A skin lesion imaged with a dermatoscope.
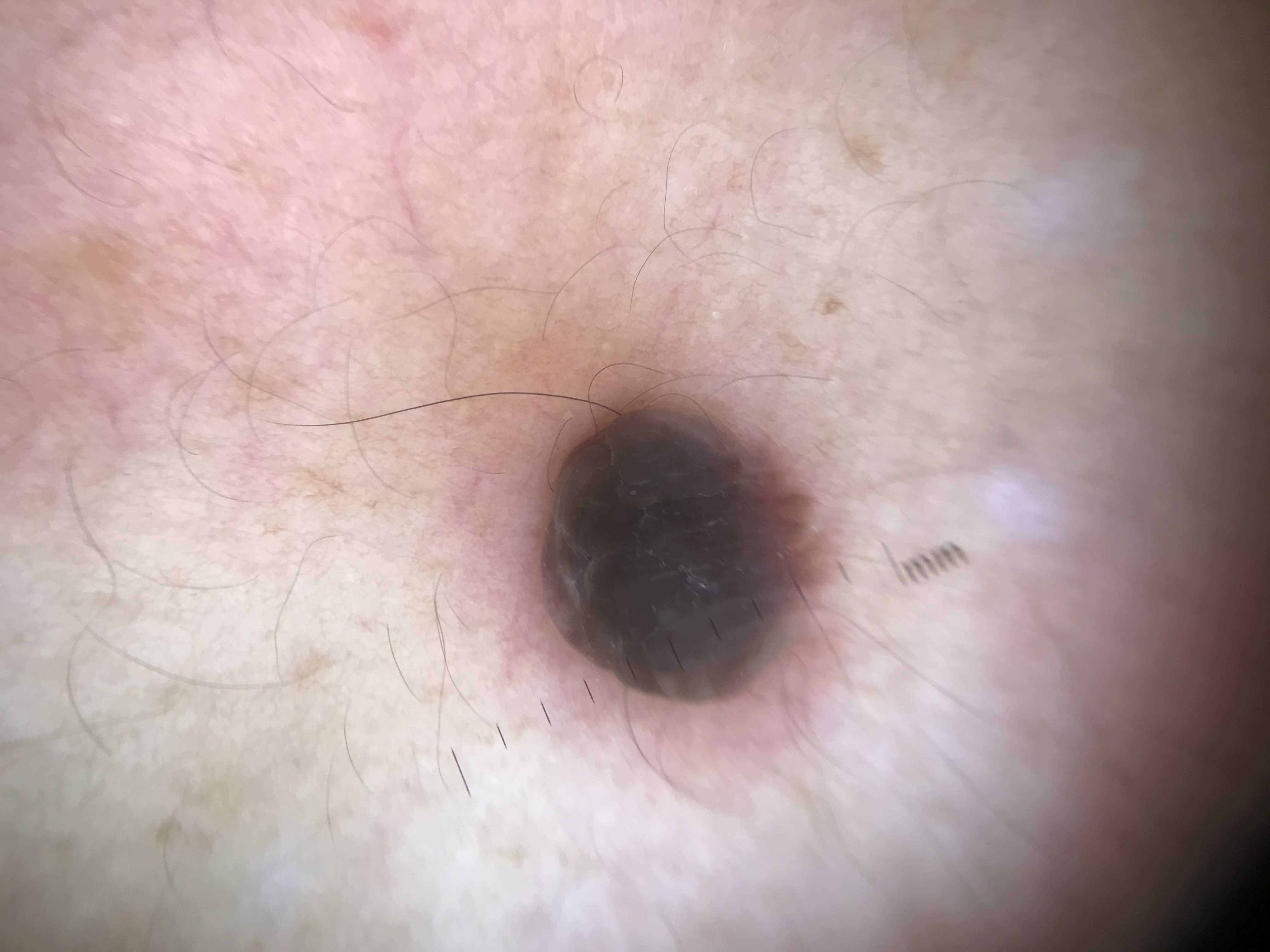Consistent with a banal lesion — a dermal nevus.